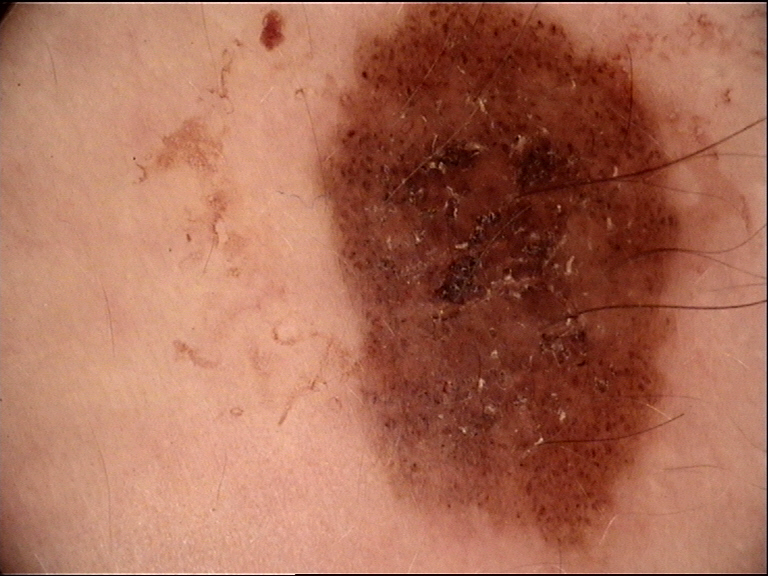imaging: dermoscopy
diagnostic label: congenital compound nevus (expert consensus)